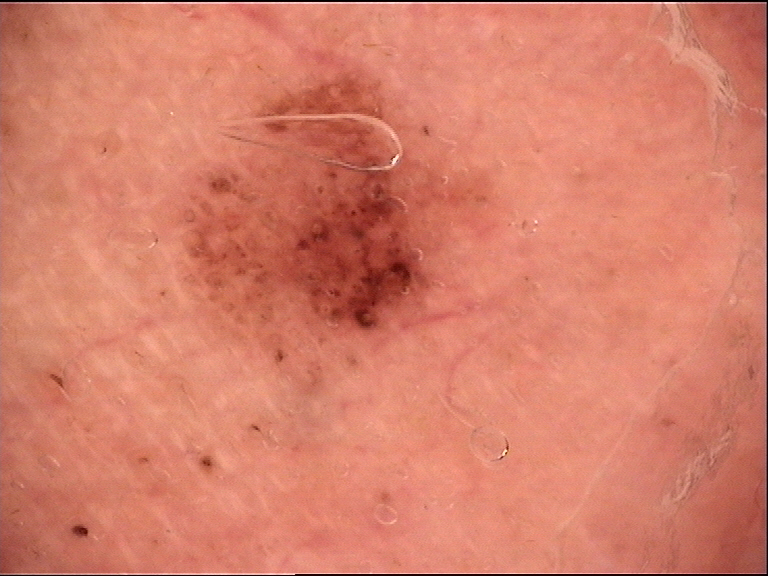Labeled as a dermal nevus.